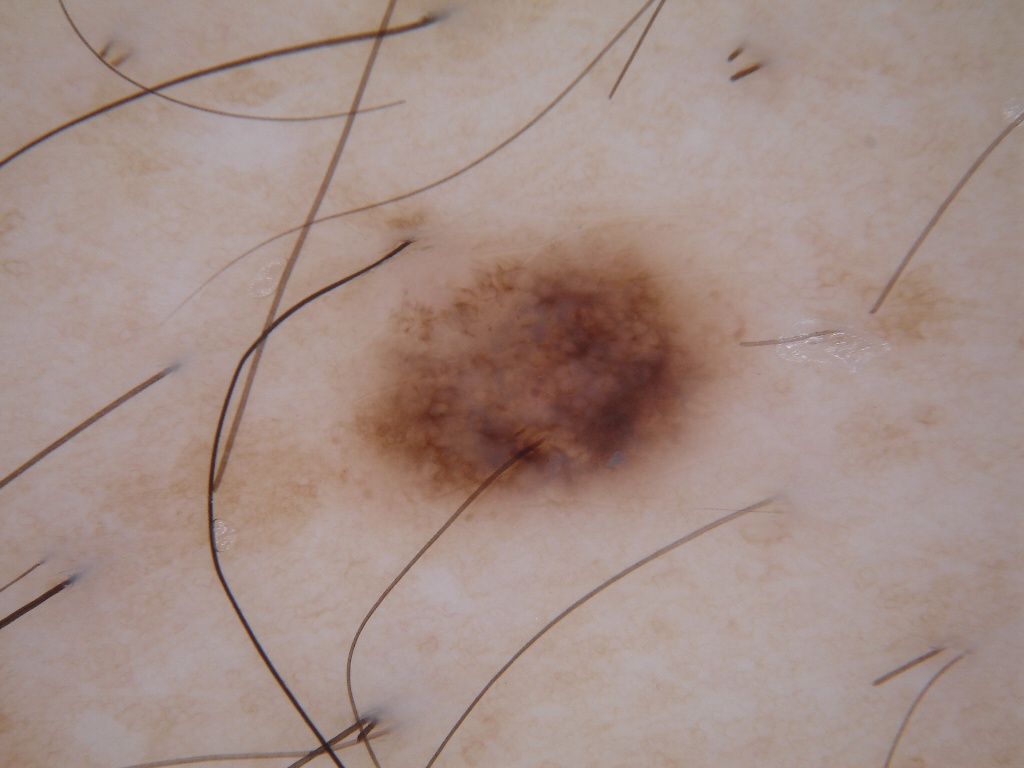The subject is a male in their mid-30s.
This is a dermoscopic photograph of a skin lesion.
Dermoscopically, the lesion shows pigment network, with no globules, negative network, milia-like cysts, or streaks.
The lesion occupies roughly 14% of the field.
As (left, top, right, bottom), the visible lesion spans 315/215/751/548.
Expert review diagnosed this as a melanocytic nevus, a benign lesion.